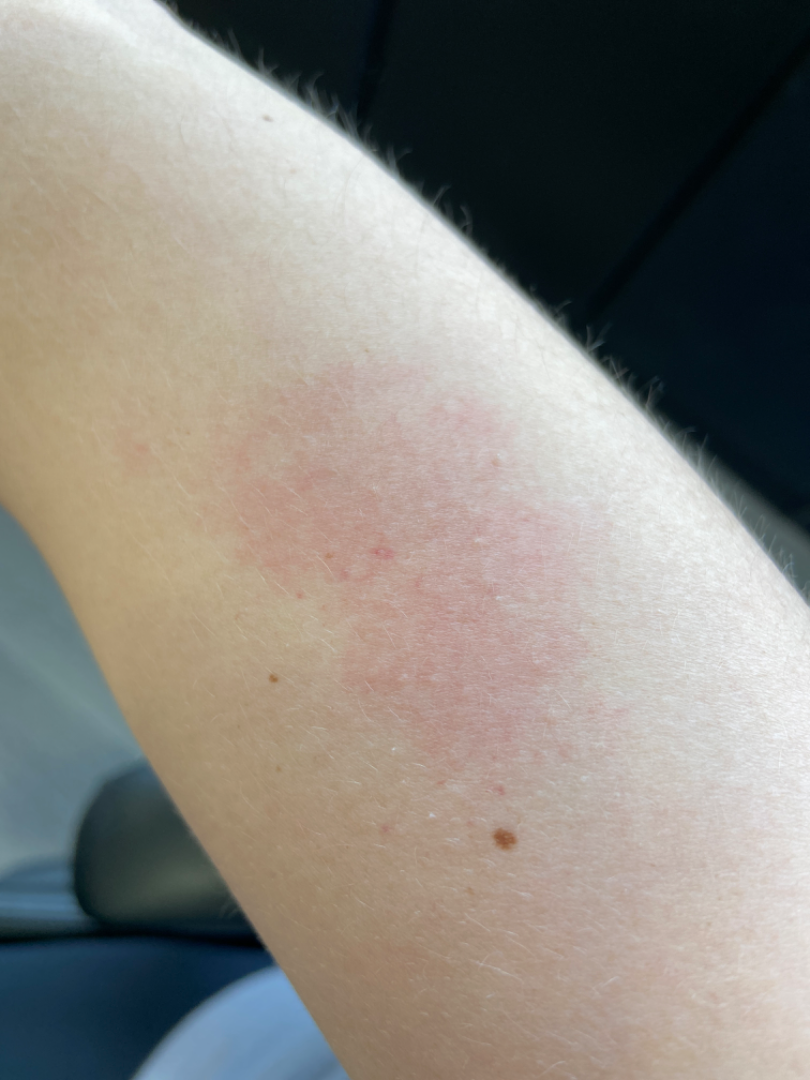Assessment:
Three independent reviewers: the differential is split between Eczema and Acute dermatitis, NOS; an alternative is Allergic Contact Dermatitis.